A dermatoscopic image of a skin lesion: 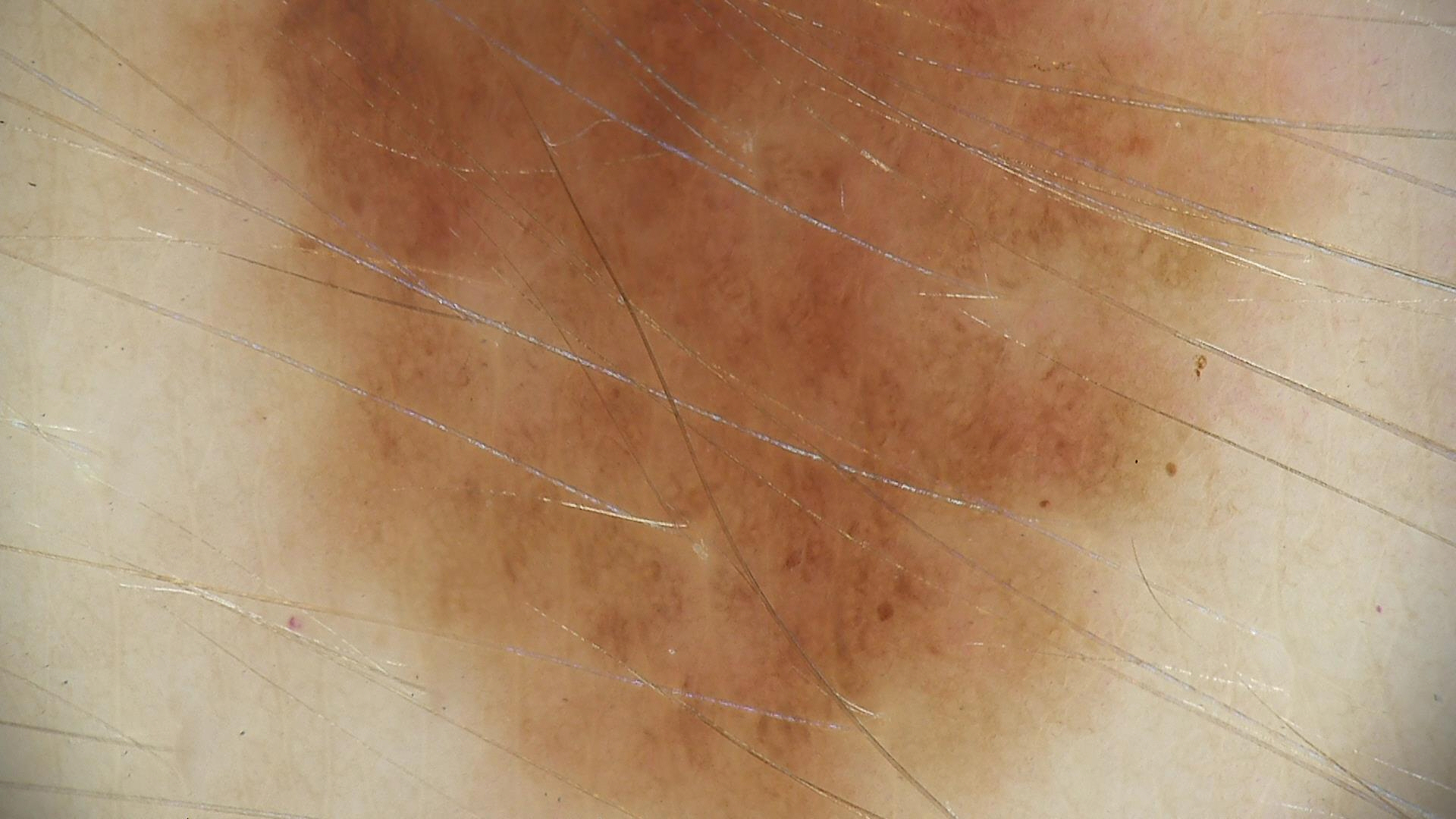Diagnosed as a benign lesion — a dysplastic junctional nevus.